The contributor is 18–29, male. The photo was captured at a distance. The arm, leg and front of the torso are involved: 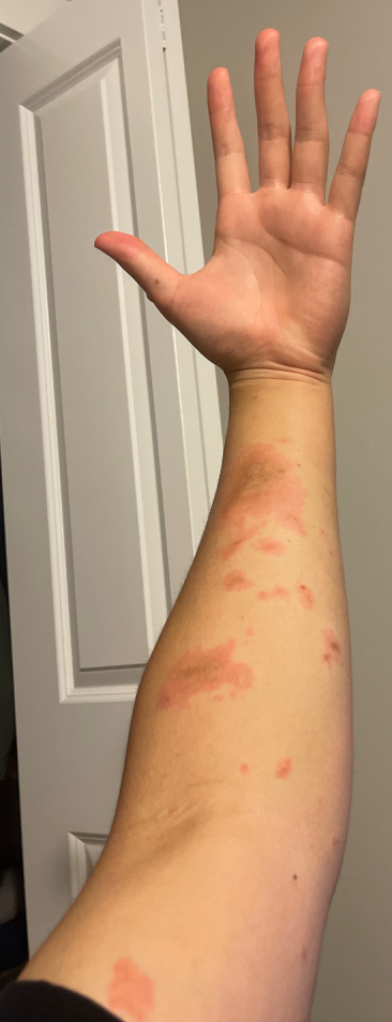Q: What symptoms does the patient report?
A: bothersome appearance, enlargement and itching
Q: Patient's own categorization?
A: a rash
Q: What conditions are considered?
A: Contact dermatitis (40%); Erythema multiforme (40%); Allergic Contact Dermatitis (20%)